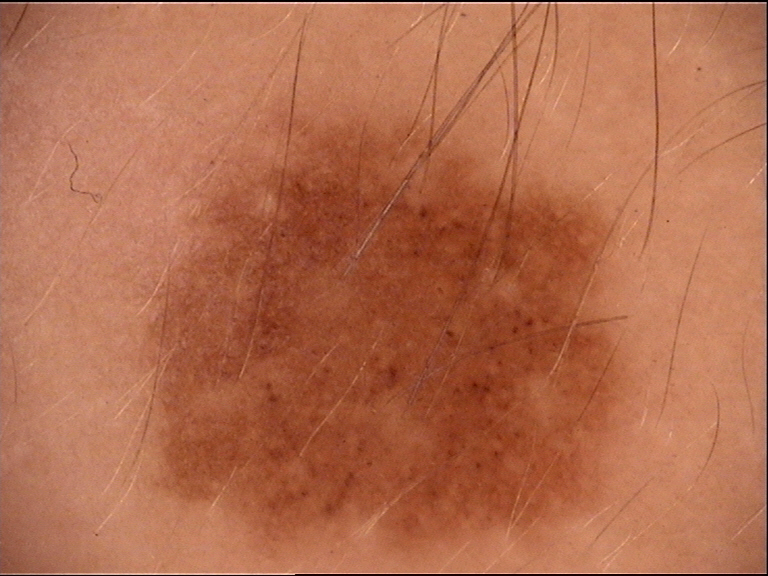assessment: dysplastic junctional nevus (expert consensus).